The affected area is the arm; the patient indicates the lesion is raised or bumpy; no relevant lesion symptoms reported; self-categorized by the patient as a growth or mole; female contributor, age 40–49; the photo was captured at a distance; the patient reported no systemic symptoms; the condition has been present for more than one year: 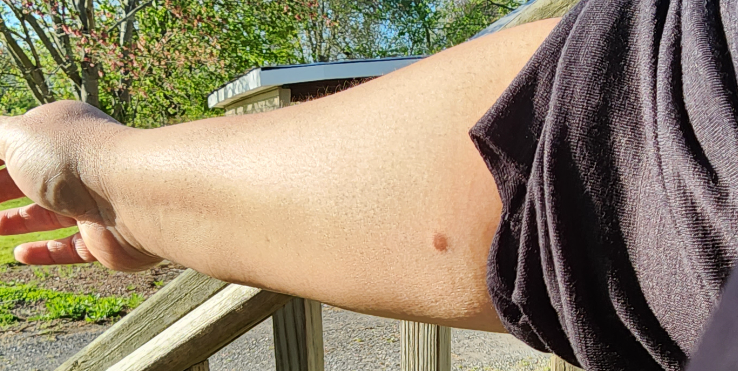| key | value |
|---|---|
| differential diagnosis | three dermatologists each reviewed the case: Dermatofibroma and Neoplasm of uncertain behavior of skin of arm were each considered, in no particular order; possibly Pseudolymphoma |